A skin lesion imaged with a dermatoscope.
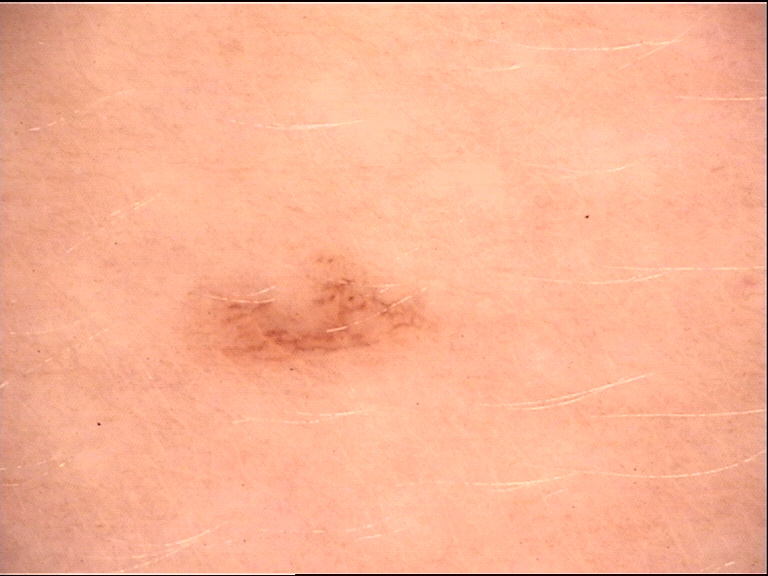Diagnosed as a dysplastic junctional nevus.